The leg is involved; the subject is a female aged 30–39; a close-up photograph.
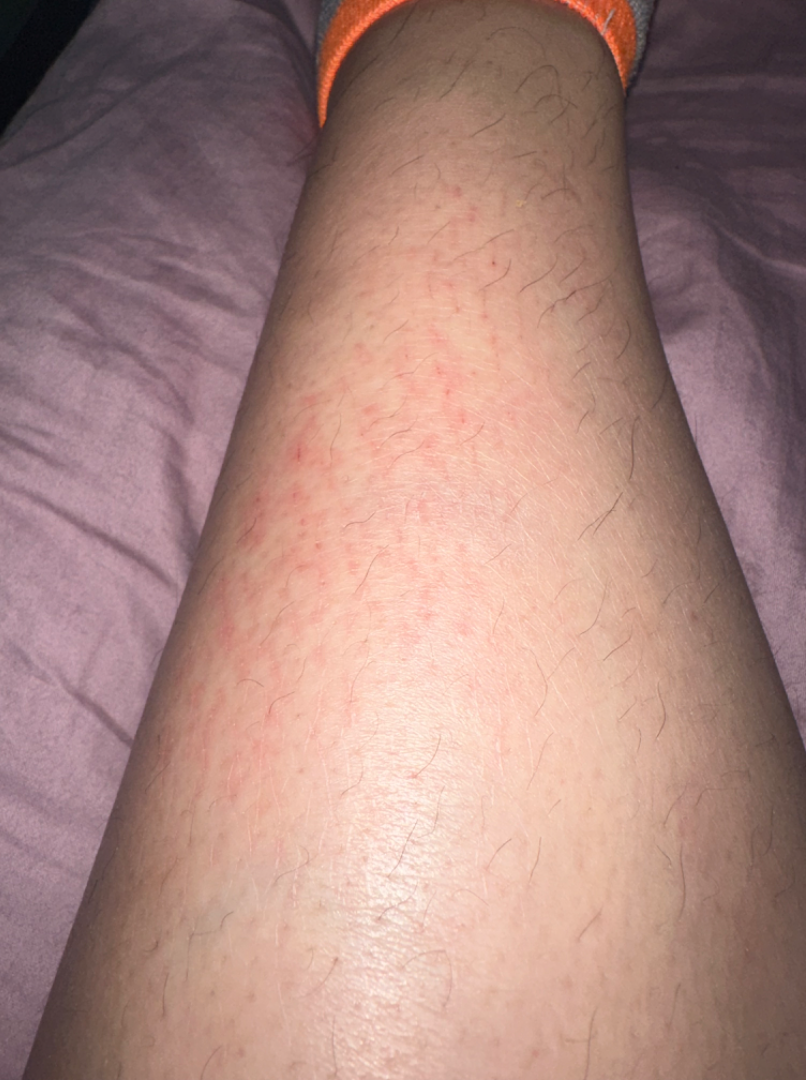| field | value |
|---|---|
| assessment | indeterminate from the photograph |
| skin tone | FST III; lay graders estimated a Monk skin tone scale of 2 |
| systemic symptoms | none reported |
| reported symptoms | itching and burning |
| texture | raised or bumpy |
| onset | less than one week |
| patient describes the issue as | a rash |